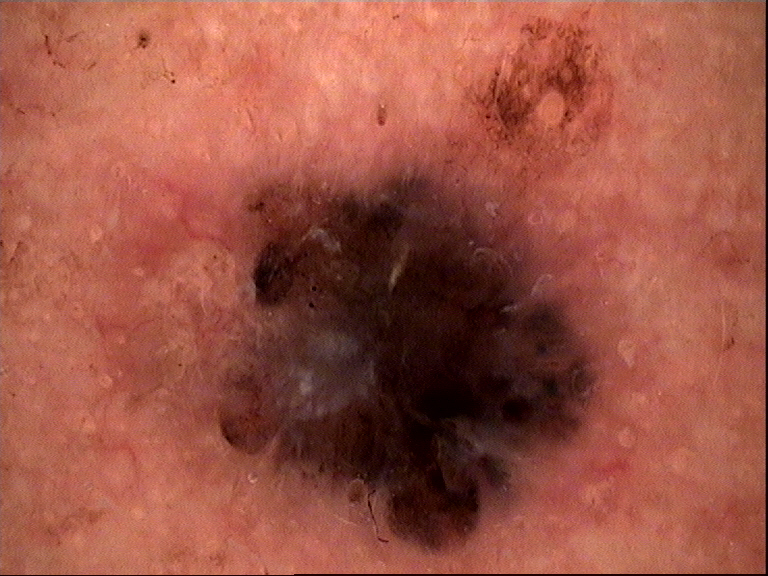Histopathologically confirmed as a keratinocytic lesion — a basal cell carcinoma.